Recorded as Fitzpatrick skin type II · a clinical close-up photograph of a skin lesion · a male subject in their early 80s · history notes prior malignancy (patient or family) and pesticide exposure:
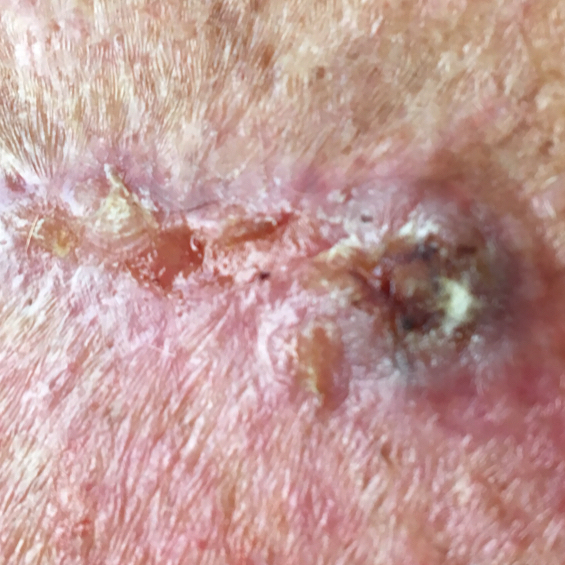{"lesion_location": "the chest", "lesion_size": {"diameter_1_mm": 32.0, "diameter_2_mm": 13.0}, "symptoms": {"present": ["elevation", "bleeding", "itching", "pain", "growth"], "absent": ["change in appearance"]}, "diagnosis": {"name": "basal cell carcinoma", "code": "BCC", "malignancy": "malignant", "confirmation": "histopathology"}}